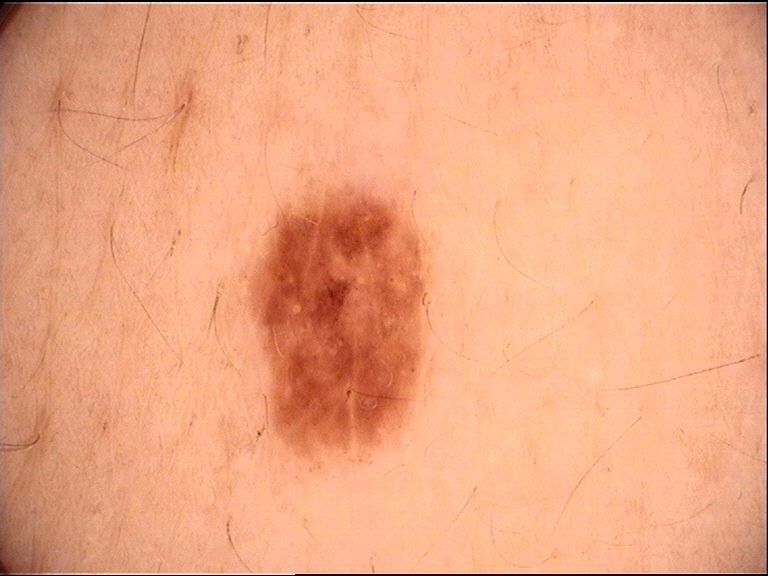diagnostic label=dysplastic junctional nevus (expert consensus).